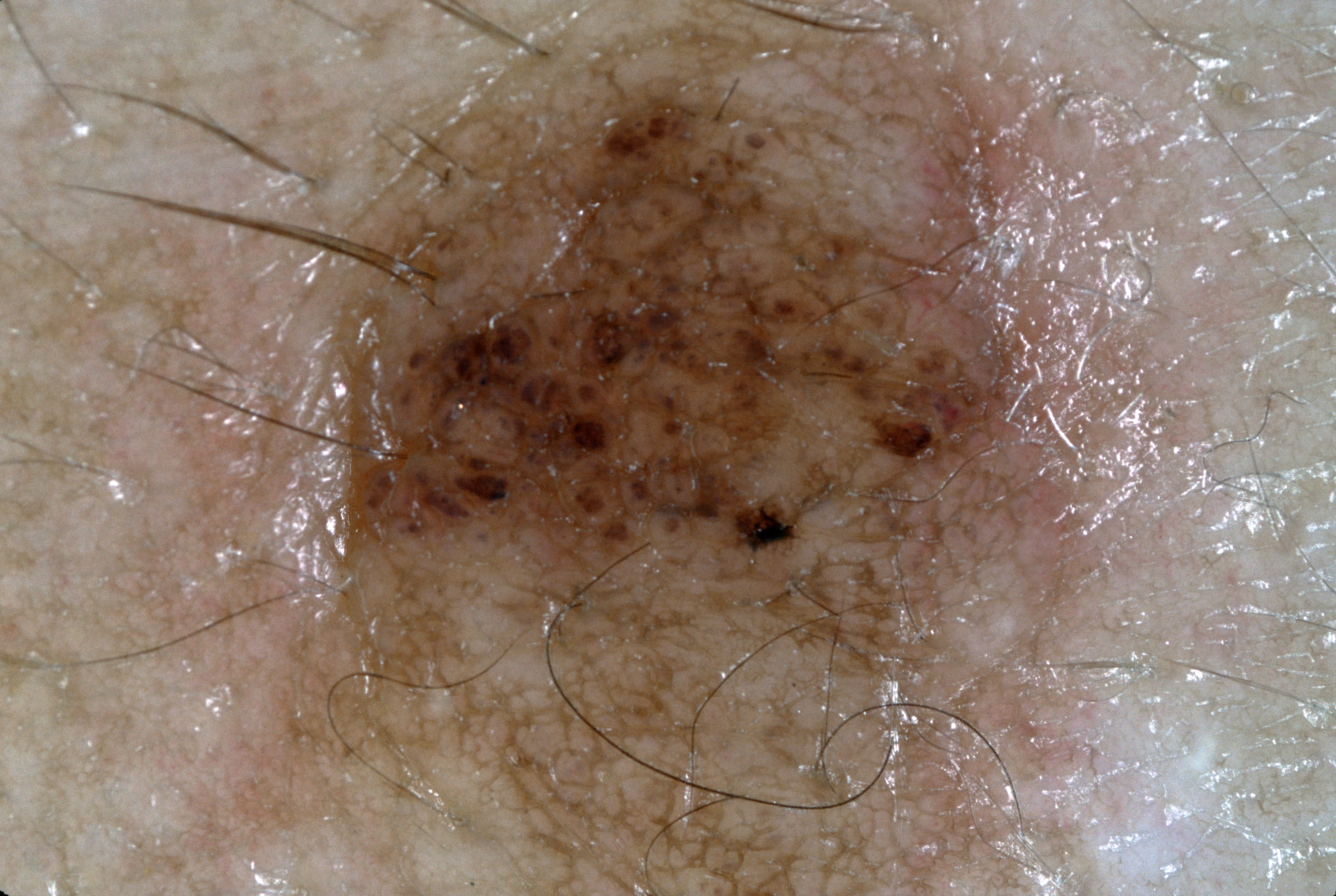Findings: A dermoscopic view of a skin lesion. Dermoscopic review identifies pigment network; no negative network, streaks, or milia-like cysts. As (left, top, right, bottom), the lesion occupies the region box(276, 7, 1130, 893). Impression: Clinically diagnosed as a melanocytic nevus.